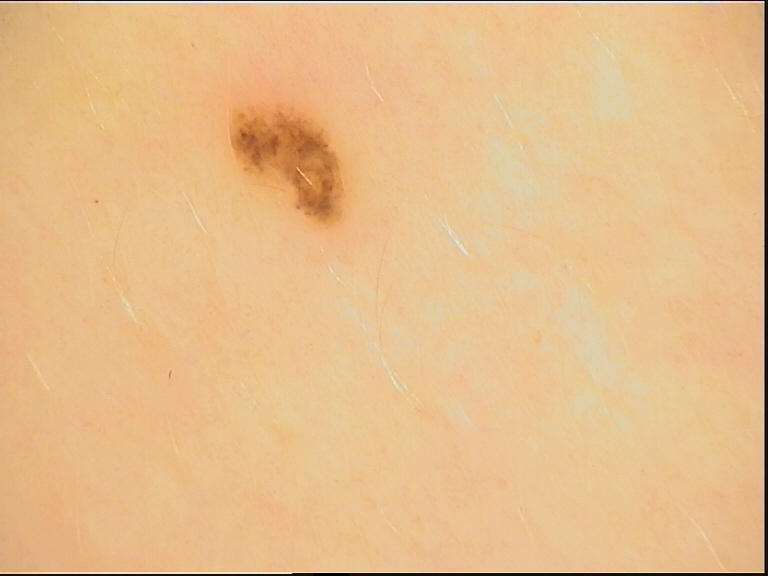Case: A dermoscopy image of a single skin lesion. Conclusion: The diagnosis was a benign lesion — a dysplastic junctional nevus.